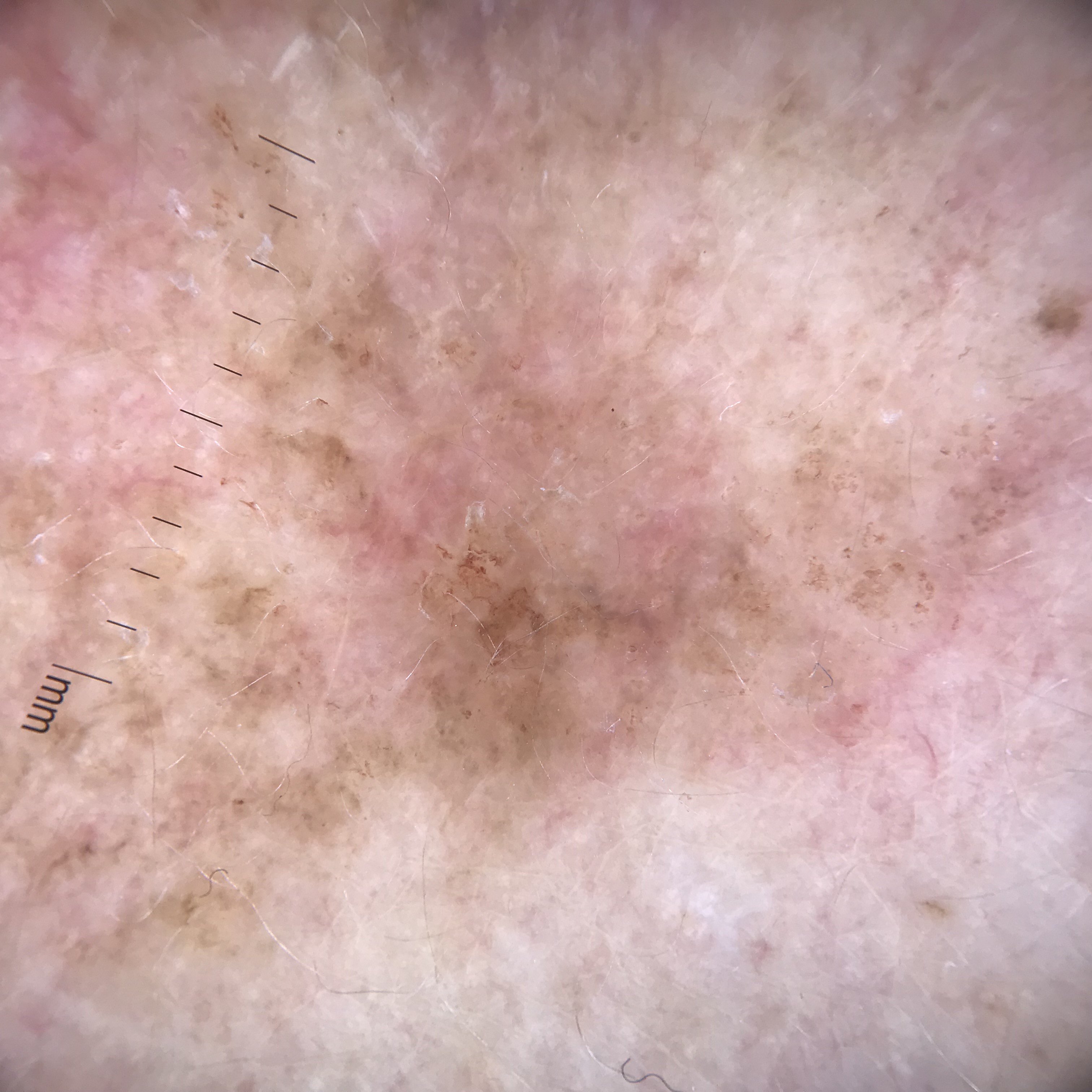The diagnosis was an actinic keratosis.